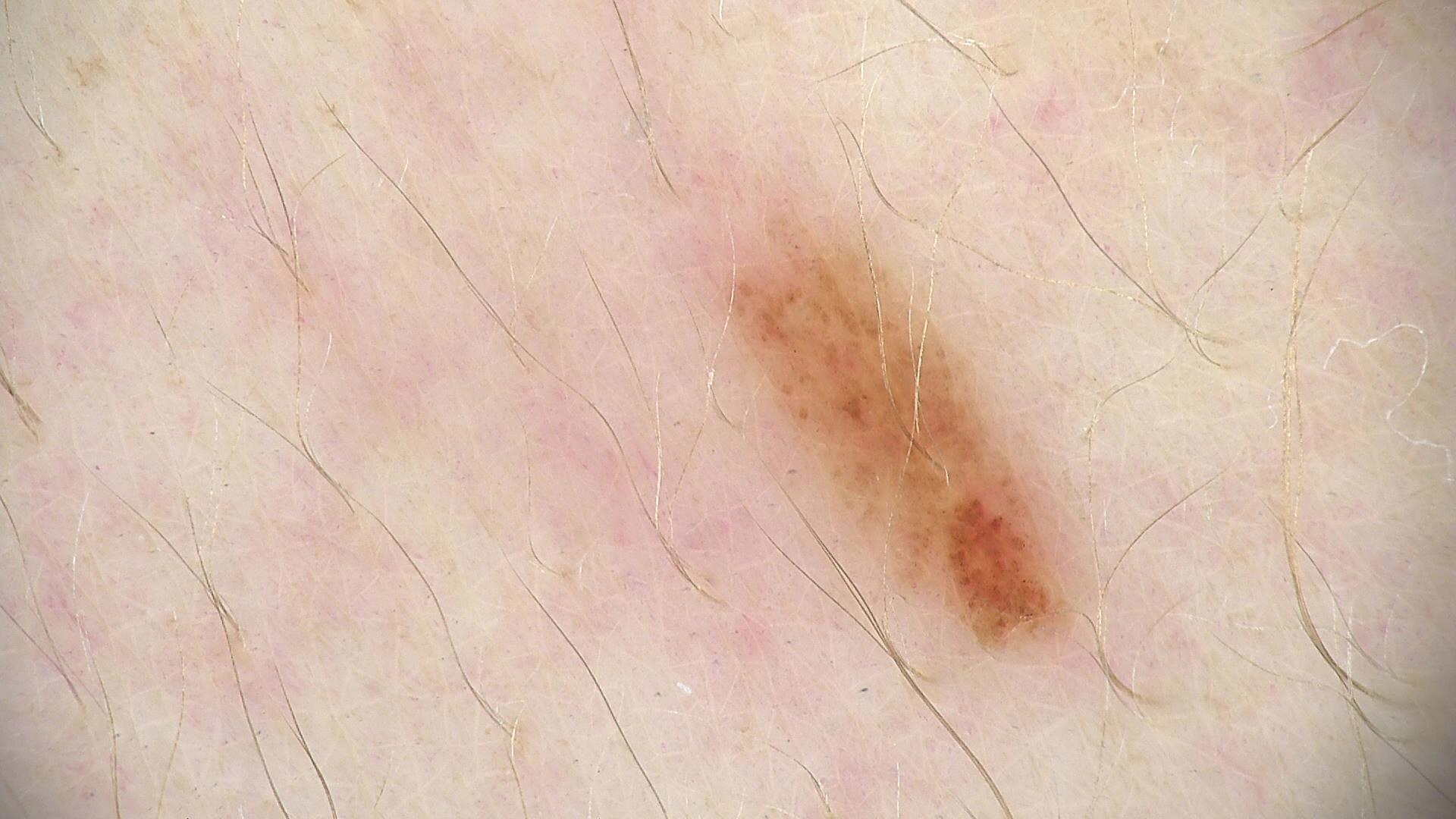Summary:
A dermoscopic close-up of a skin lesion.
Impression:
Consistent with a benign lesion — a dysplastic junctional nevus.